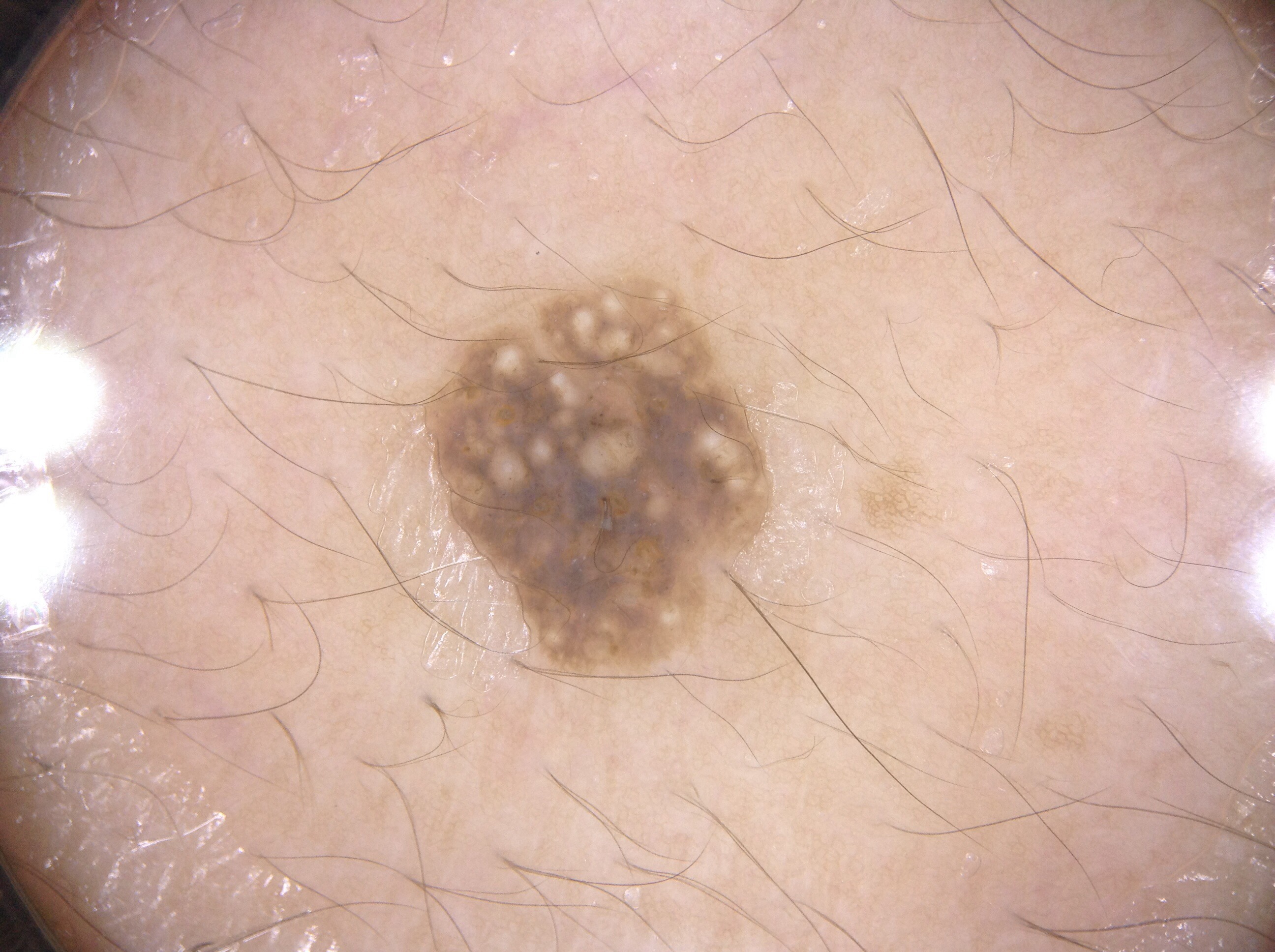The patient is a female approximately 65 years of age. This is a dermoscopic photograph of a skin lesion. The lesion's extent is left=428, top=290, right=767, bottom=669. The lesion is small relative to the field of view. Dermoscopy demonstrates milia-like cysts. Consistent with a seborrheic keratosis, a benign skin lesion.